Female patient, age 30–39. The affected area is the leg. Self-categorized by the patient as a rash. Texture is reported as raised or bumpy and rough or flaky. The contributor notes itching. The patient also reports fatigue. The condition has been present for one to four weeks. The photograph is a close-up of the affected area: 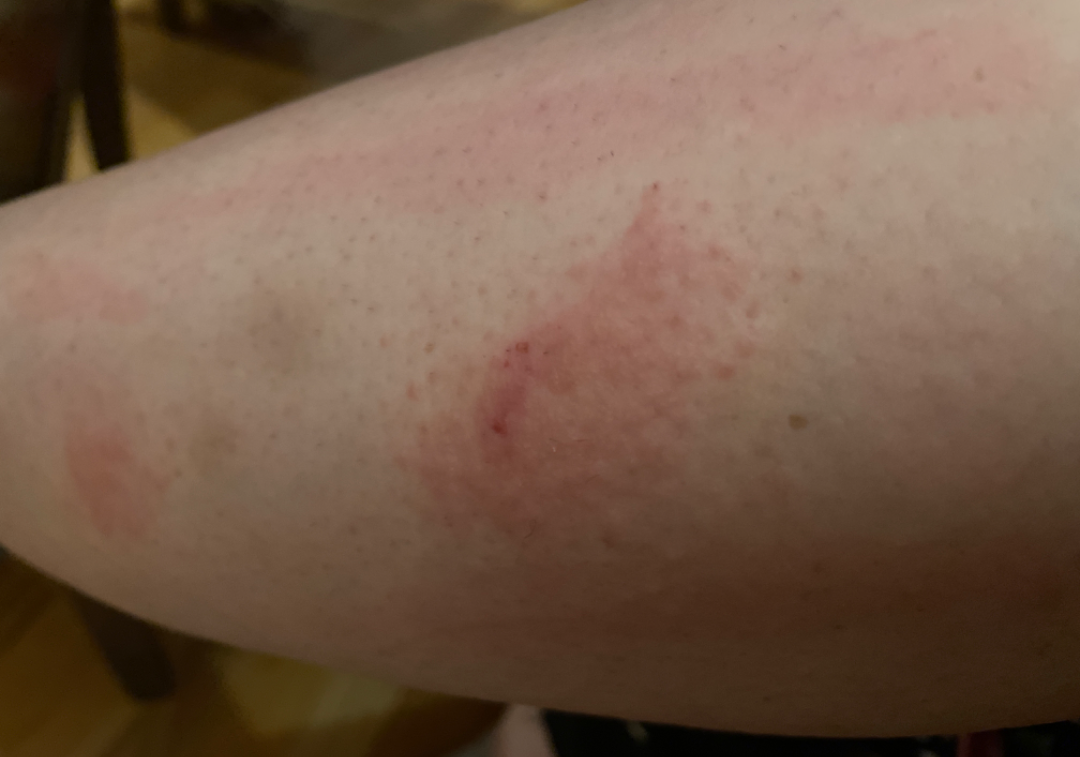Diagnostic features were not clearly distinguishable in this photograph.